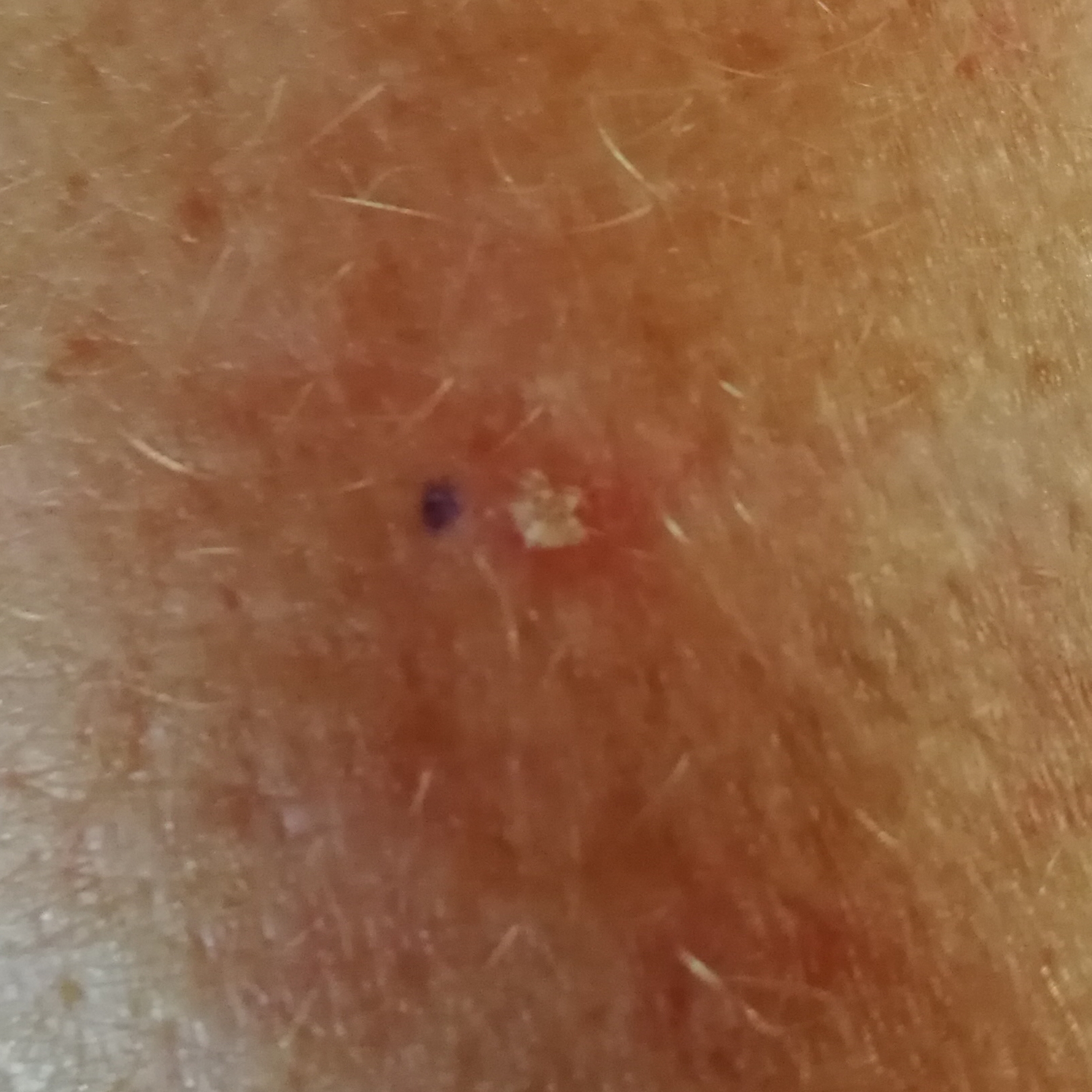A patient aged 67. A smartphone photograph of a skin lesion. The lesion involves a forearm. The diagnostic impression was a lesion with uncertain malignant potential — an actinic keratosis.